The affected area is the arm; the subject is 30–39, male; the photo was captured at a distance.
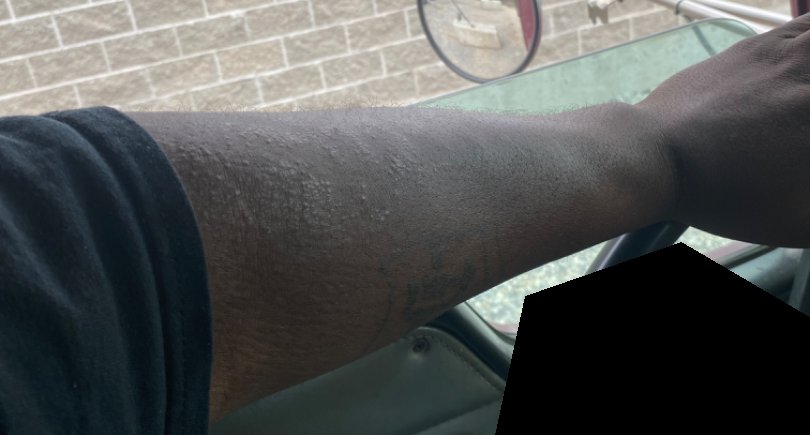Skin tone: FST IV; lay graders estimated Monk Skin Tone 6 (US pool) or 4 (India pool). Reported duration is one to three months. Symptoms reported: itching. The patient considered this a rash. The lesion is described as raised or bumpy. Chronic dermatitis, NOS and Amyloidosis of skin were considered with similar weight; a more distant consideration is Lichen Simplex Chronicus; less likely is Lichen planus/lichenoid eruption; less probable is Eczema.